Dermoscopy of a skin lesion:
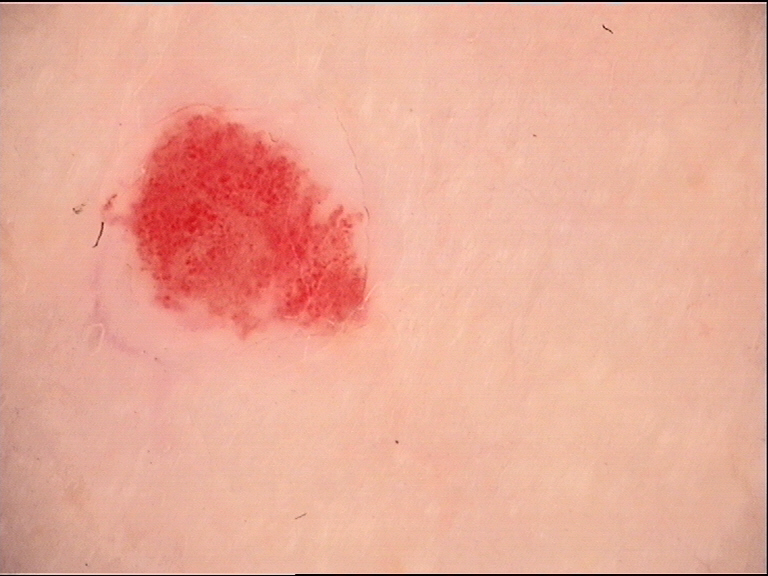Case: The architecture is that of a vascular lesion. Conclusion: Classified as a hemangioma.